A skin lesion imaged with a dermatoscope.
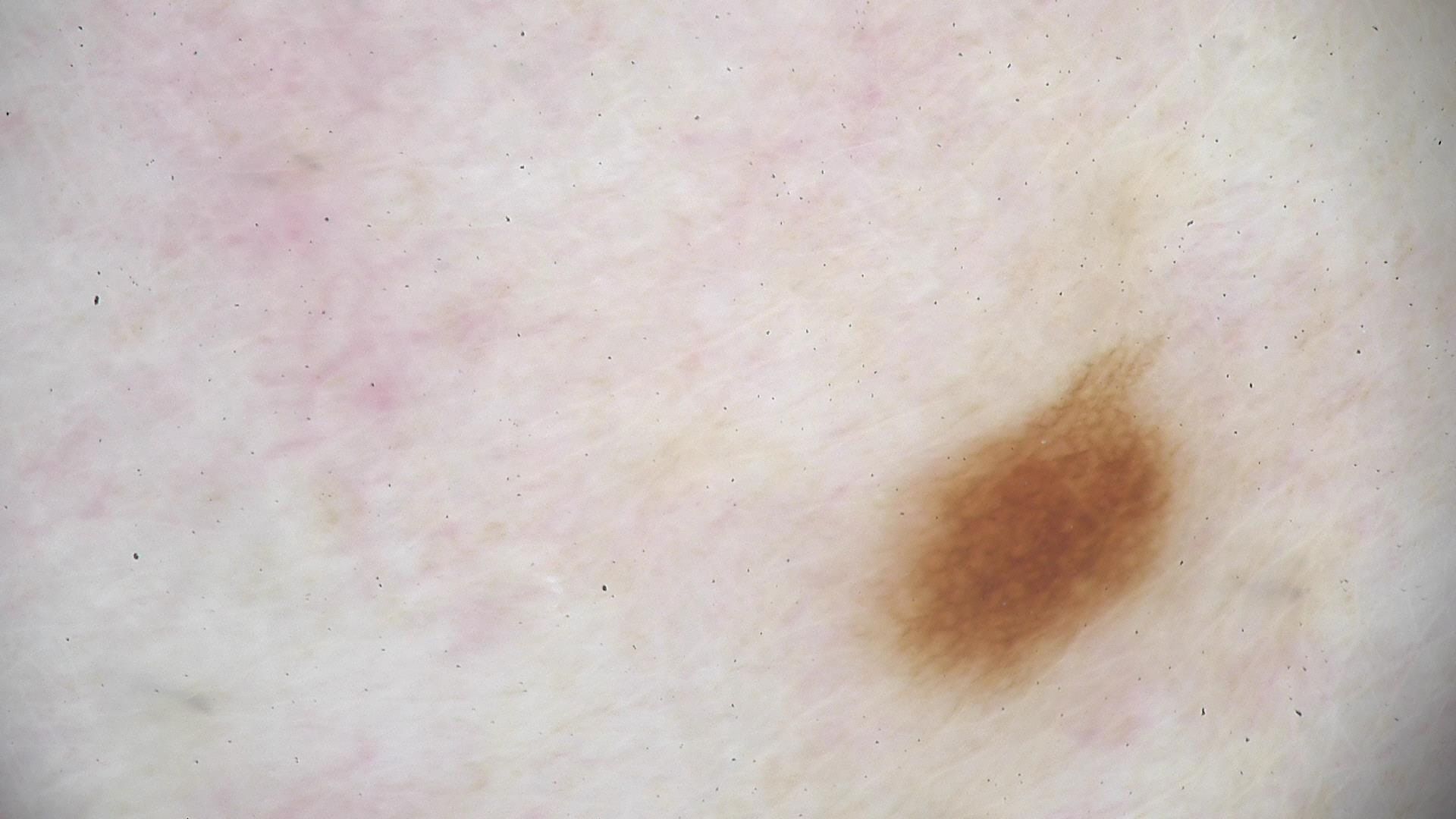diagnostic label: dysplastic junctional nevus (expert consensus).